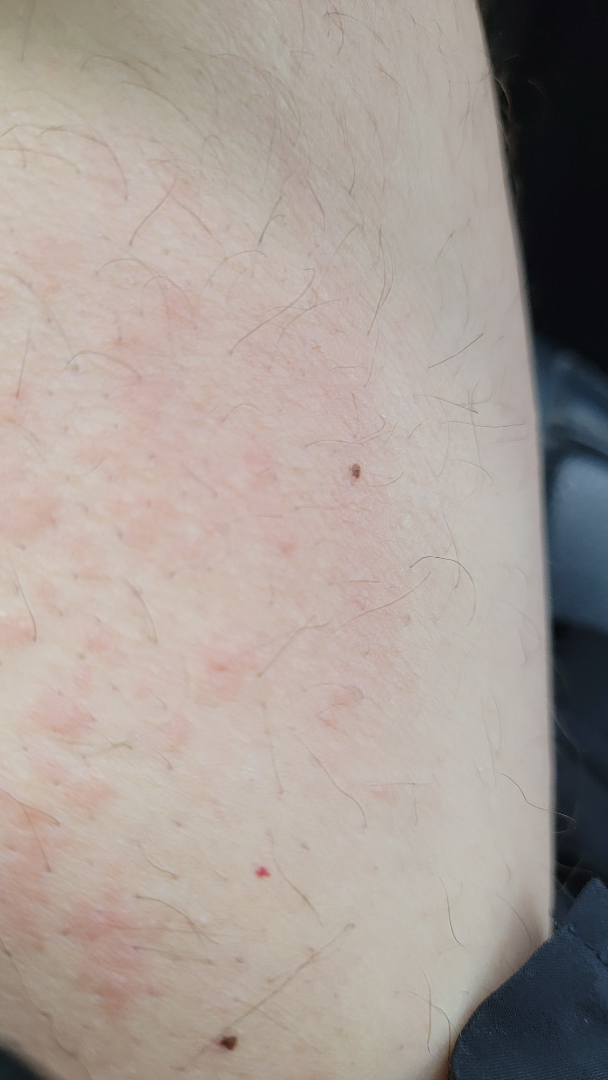affected area = leg; skin tone = lay reviewers estimated 2 on the Monk Skin Tone; framing = close-up; onset = one to four weeks; differential diagnosis = the impression was split between Urticaria, Eczema and Allergic Contact Dermatitis.